The photo was captured at an angle · the affected area is the leg — 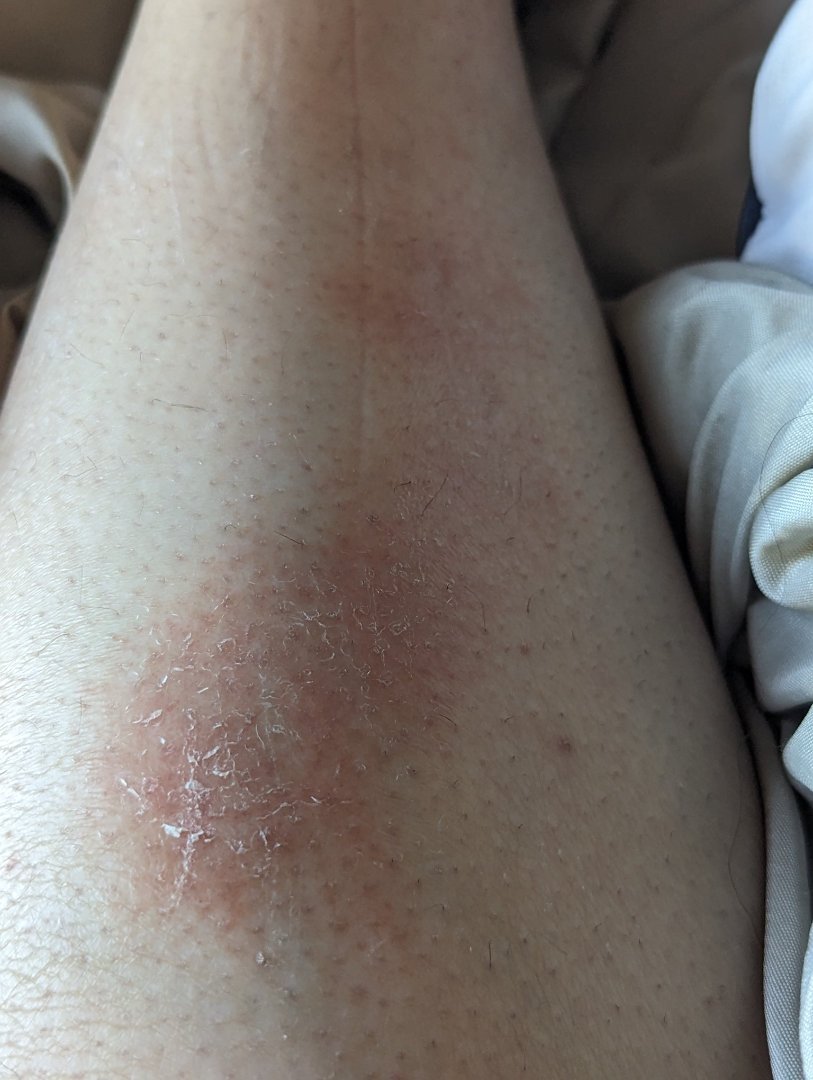Case summary:
* patient-reported symptoms · itching, enlargement and bothersome appearance
* patient's own categorization · a rash
* duration · one to four weeks
* diagnostic considerations · one reviewing dermatologist: the differential is split between Pigmented purpuric eruption and Erythema nodosum